The patient is a male aged 40–49, the photo was captured at an angle, located on the palm and back of the hand:
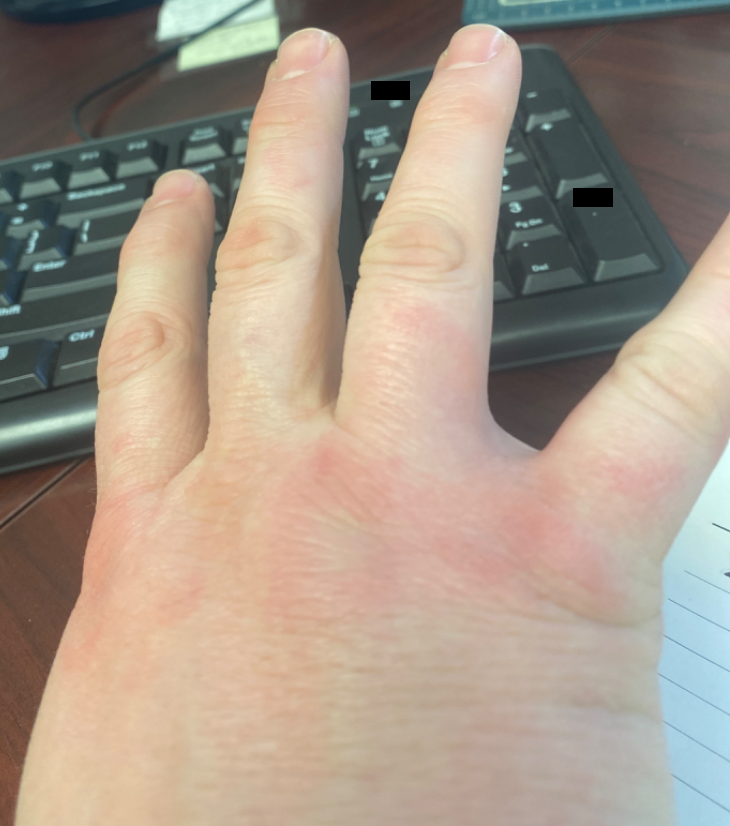The differential, in no particular order, includes Eczema and Granuloma annulare.